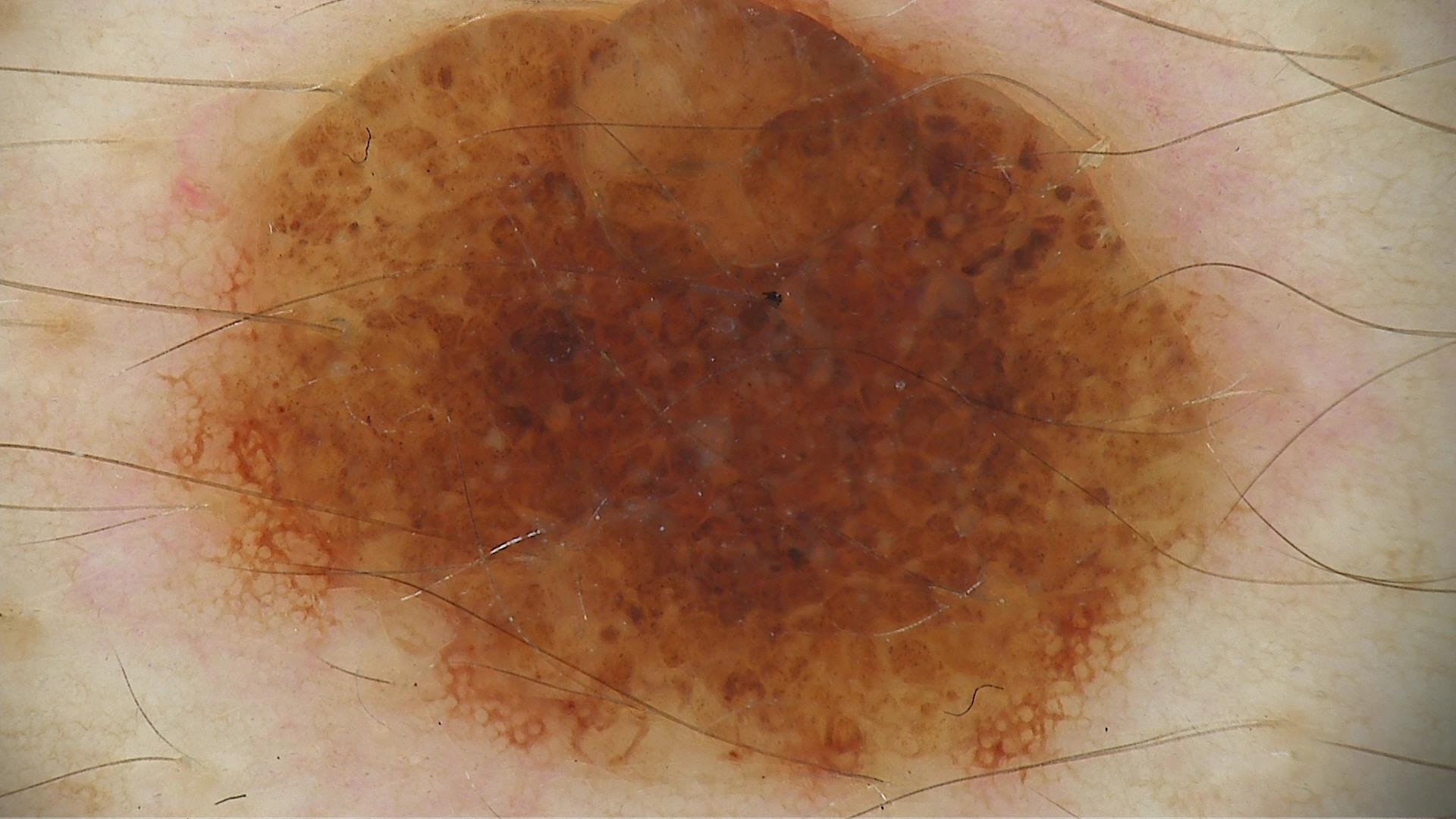  image: dermoscopy
  lesion_type:
    main_class: banal
    pattern: compound
  diagnosis:
    name: compound nevus
    code: cb
    malignancy: benign
    super_class: melanocytic
    confirmation: expert consensus